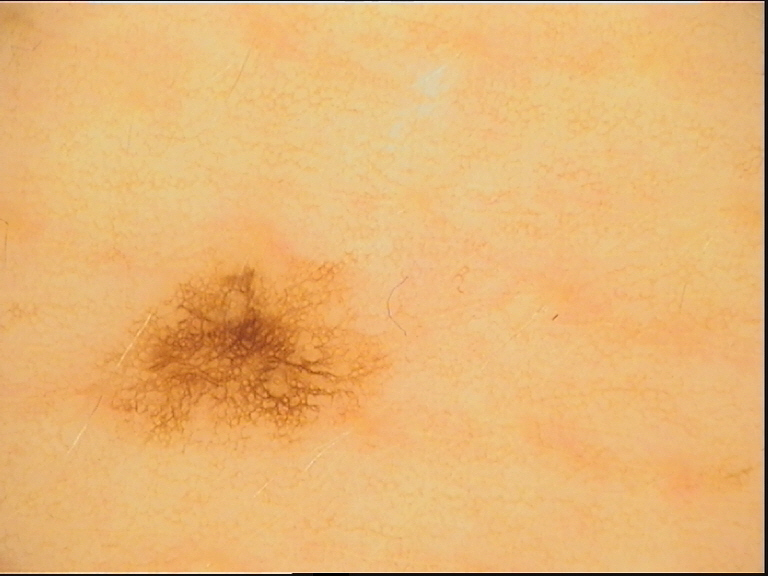Q: What is the diagnosis?
A: junctional nevus (expert consensus)